Texture is reported as rough or flaky; this image was taken at an angle.
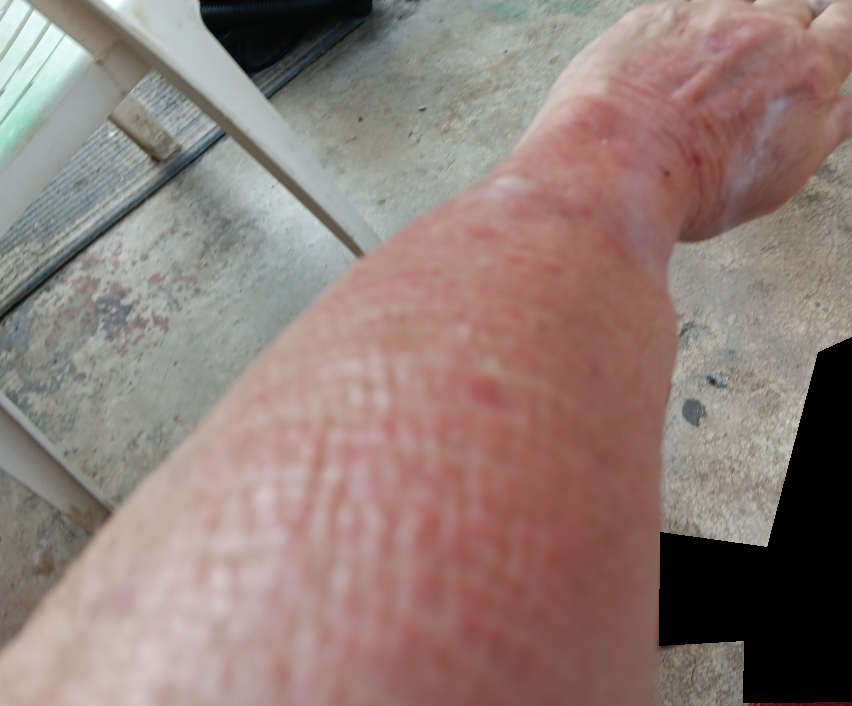dermatologist impression = SCC/SCCIS (favored).